The arm is involved, texture is reported as raised or bumpy, the condition has been present for less than one week, skin tone: Fitzpatrick skin type I; non-clinician graders estimated a Monk skin tone scale of 2, close-up view — 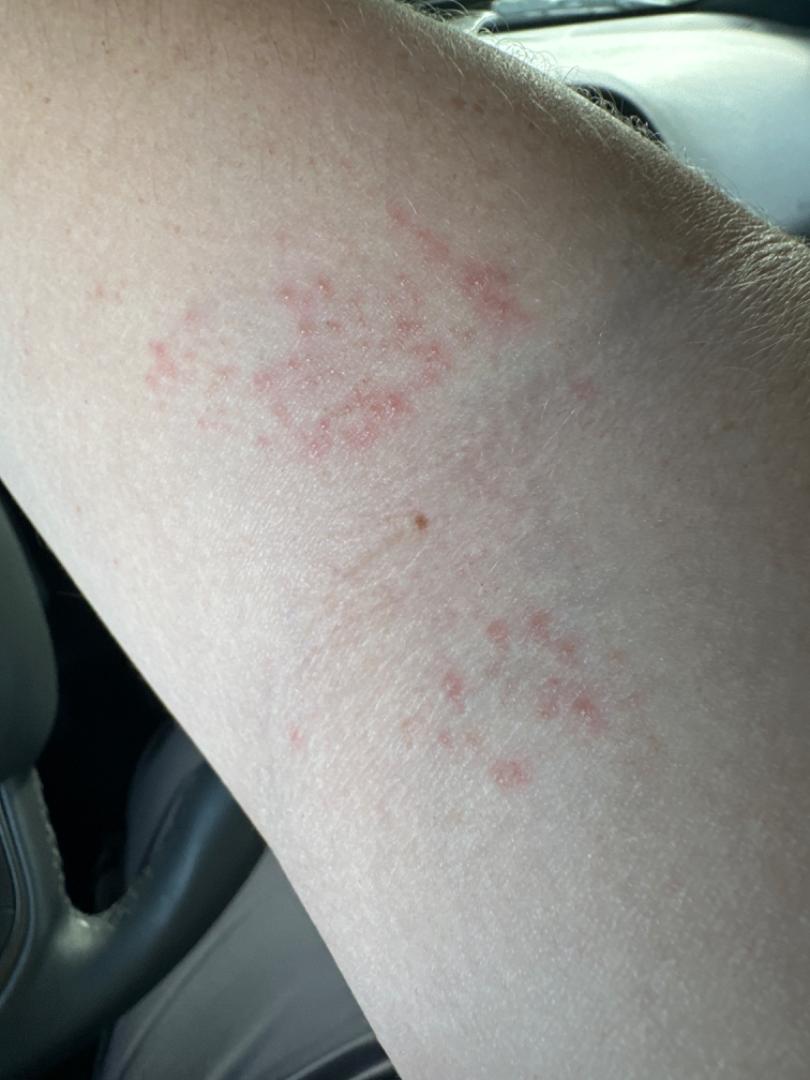<summary>
  <differential>
    <tied_lead>Eczema, Allergic Contact Dermatitis</tied_lead>
    <unlikely>Irritant Contact Dermatitis</unlikely>
  </differential>
</summary>